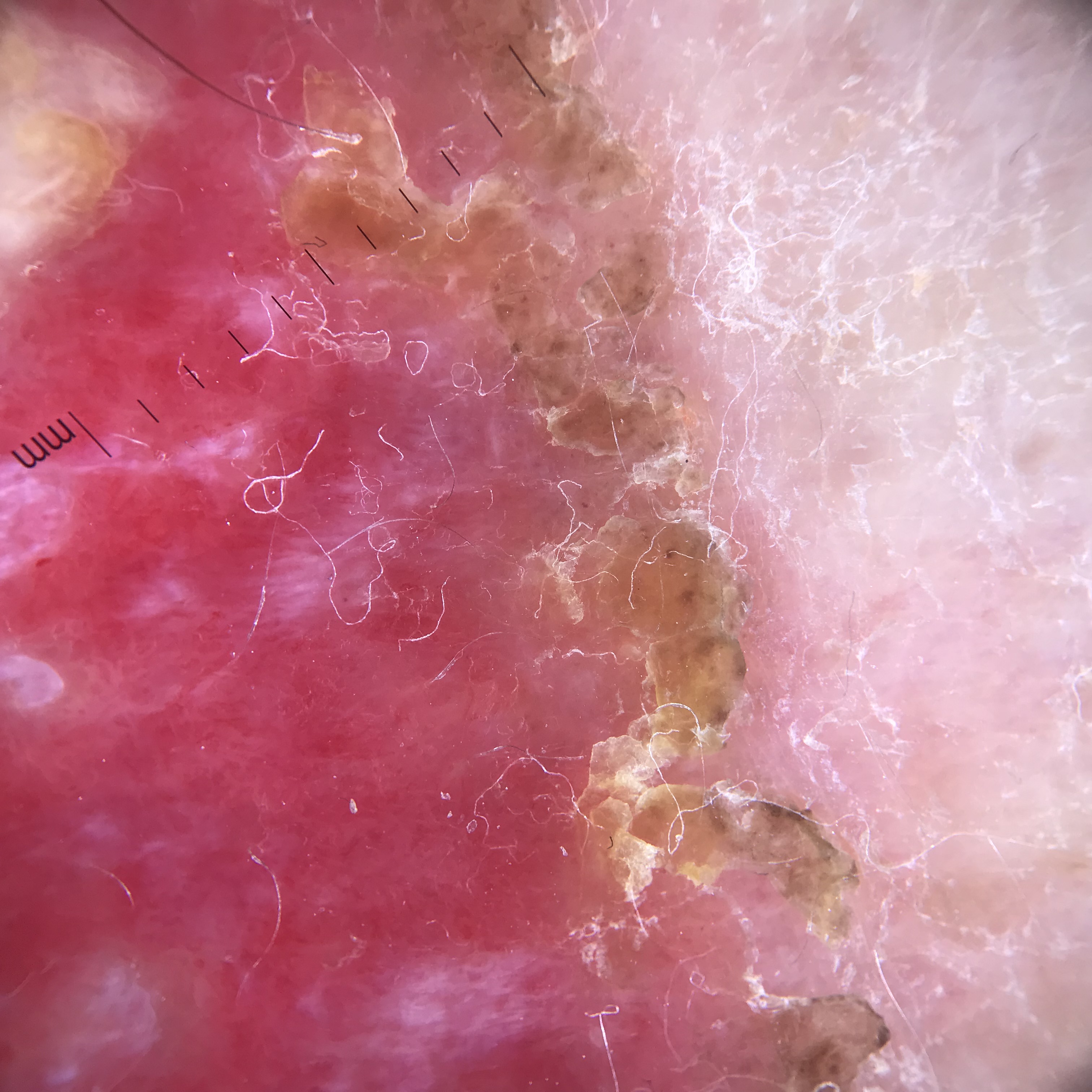imaging=dermatoscopy | category=keratinocytic | class=Bowen's disease (biopsy-proven).